The affected area is the back of the torso. The subject is a male aged 30–39. The photograph is a close-up of the affected area:
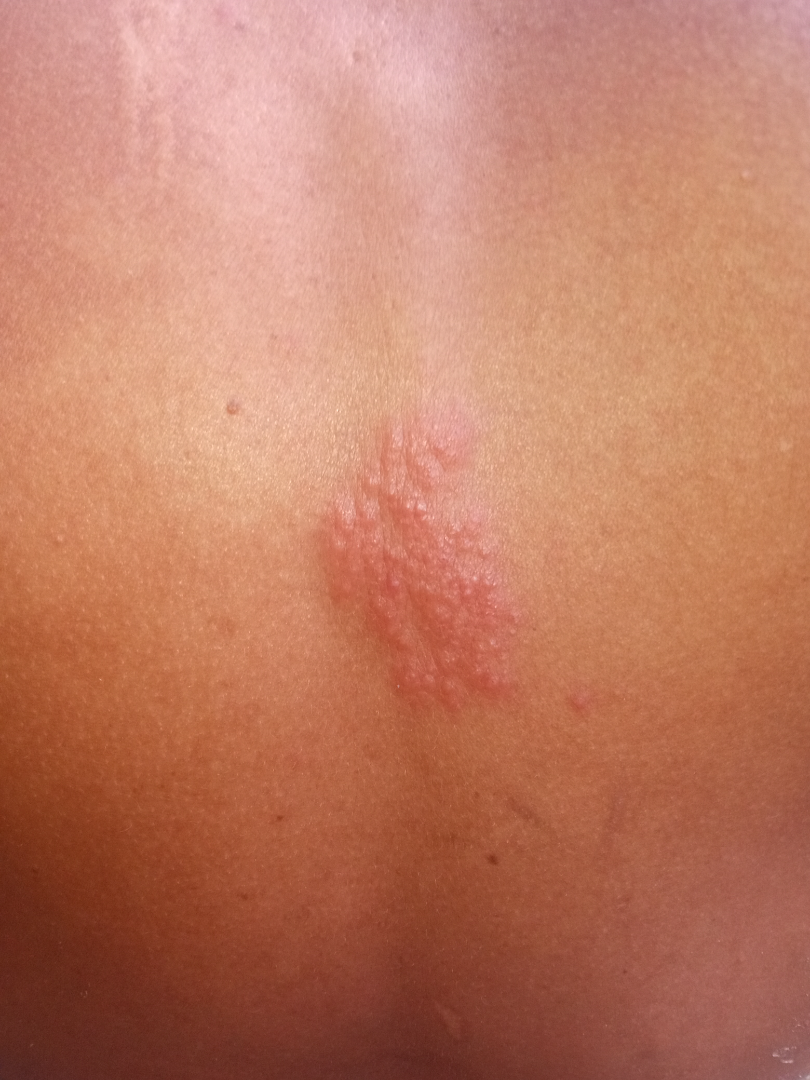The lesion is described as raised or bumpy and fluid-filled. Fitzpatrick III; lay reviewers estimated MST 2 (US pool) or 3 (India pool). Self-categorized by the patient as skin that appeared healthy to them. No relevant systemic symptoms. Present for one to four weeks. The reviewing clinician's impression was: most consistent with Allergic Contact Dermatitis; with consideration of Herpes Simplex.